Acquired for a research image collection, with no referral diagnosis; few moles overall by the patient's own estimate; a clinical photograph showing a skin lesion; on a questionnaire the patient reported a personal history of cancer, no immunosuppression, and no prior organ transplant:
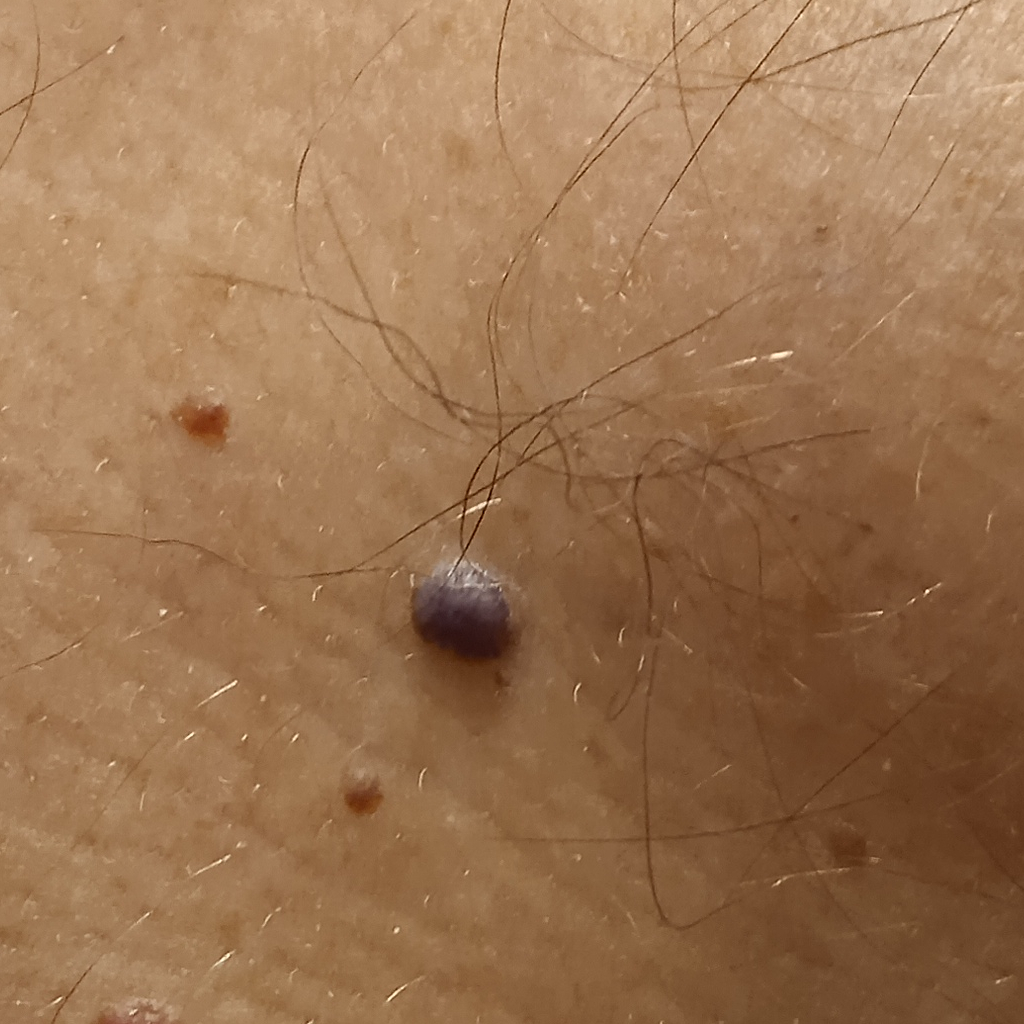<skin_lesion>
  <lesion_location>the torso</lesion_location>
  <lesion_size>
    <diameter_mm>4.7</diameter_mm>
  </lesion_size>
  <diagnosis>
    <name>angioma</name>
    <malignancy>benign</malignancy>
  </diagnosis>
</skin_lesion>